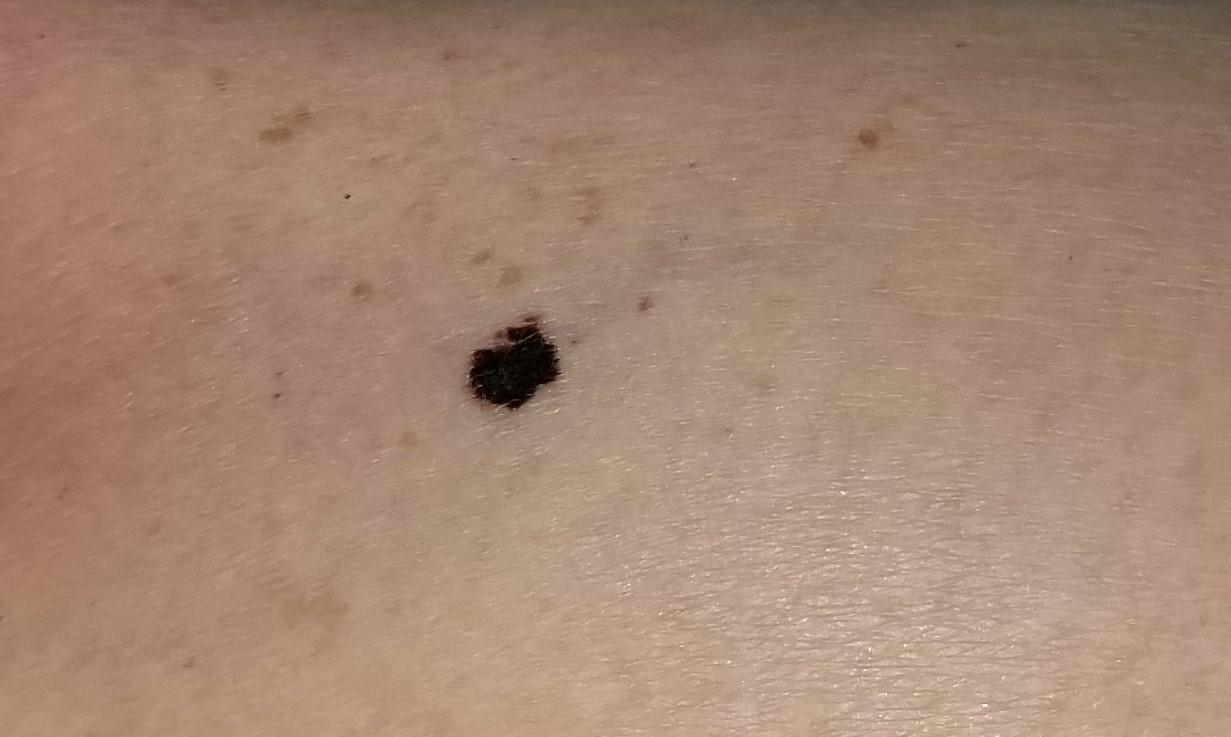Conclusion: Histopathologically confirmed as a melanoma.